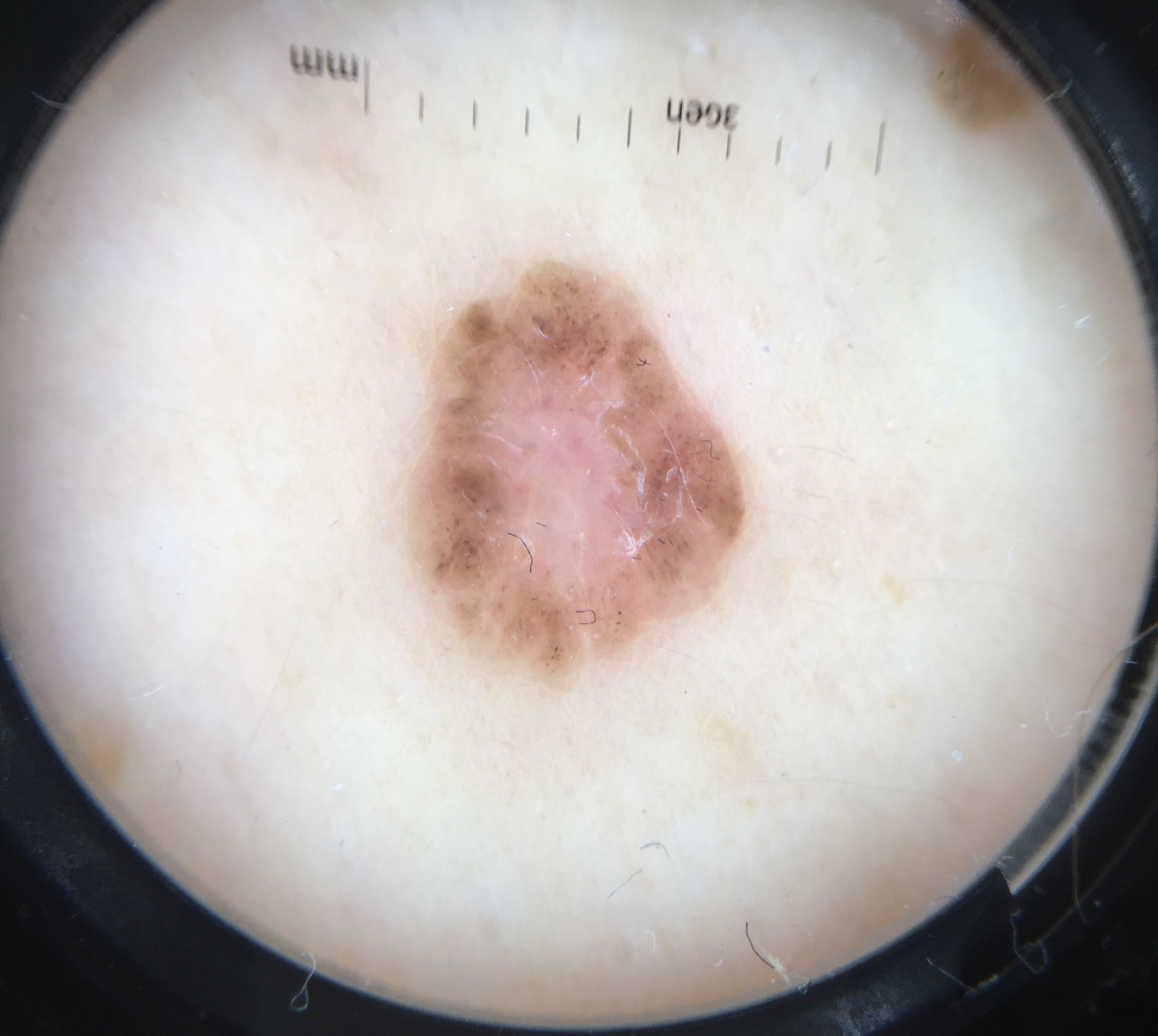* image type: dermatoscopy
* pathology: basal cell carcinoma (biopsy-proven)